The patient considered this a rash · the lesion is described as rough or flaky · the front of the torso, top or side of the foot and leg are involved · reported lesion symptoms include burning, itching and pain · the condition has been present for less than one week · the photograph was taken at an angle.
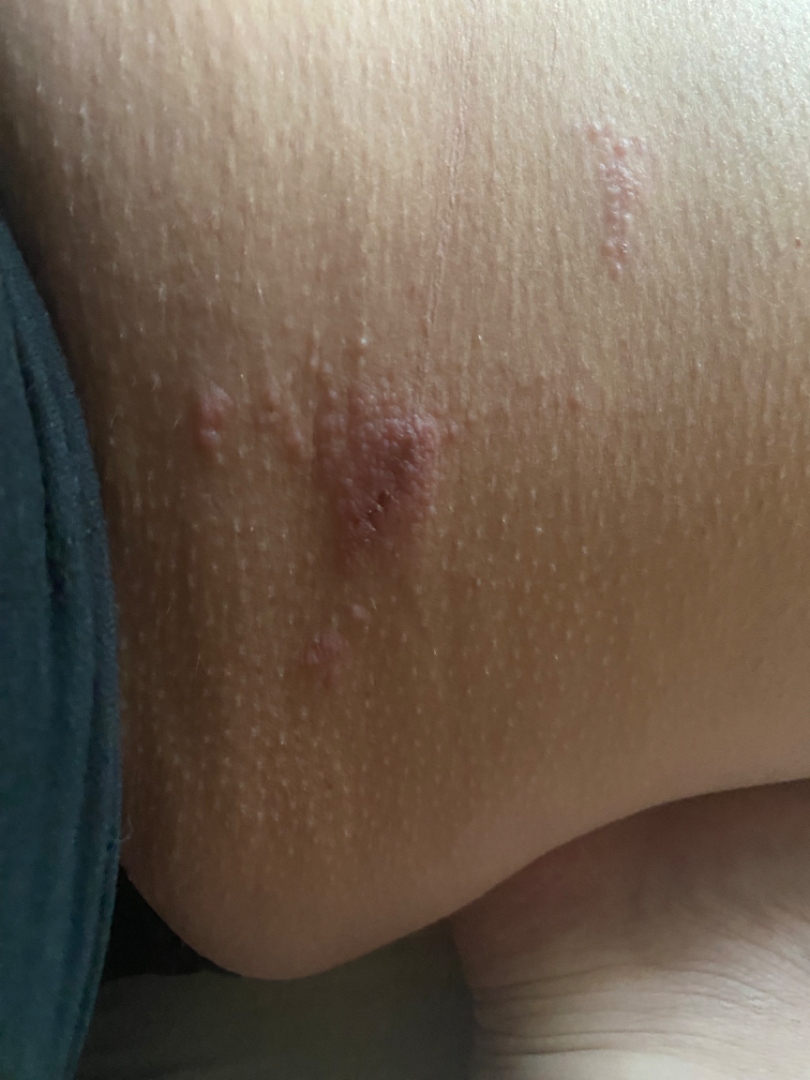Case summary:
– assessment · not assessable